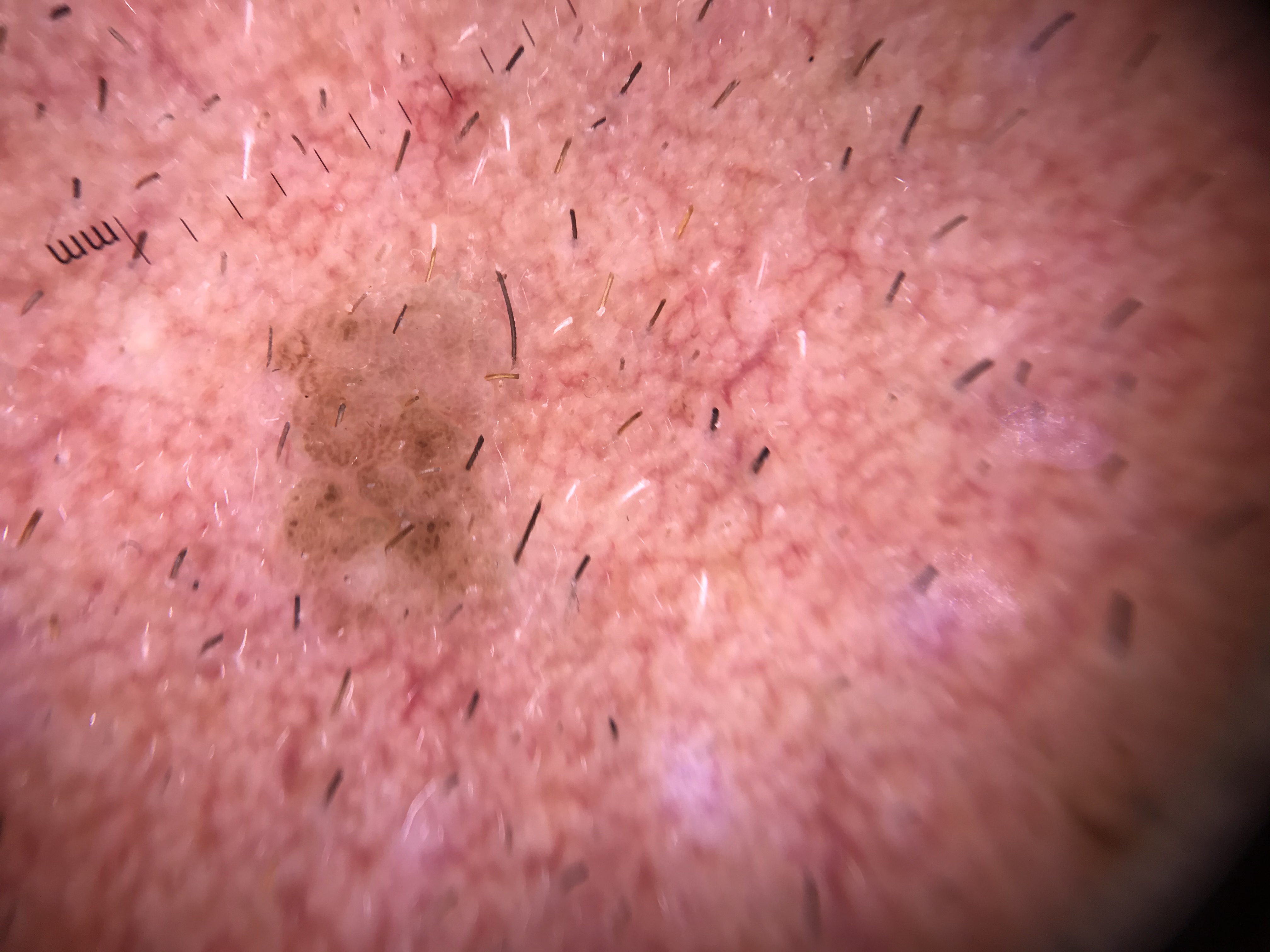image: dermoscopy, diagnostic label: seborrheic keratosis (expert consensus).